This is a close-up image, texture is reported as raised or bumpy, no associated systemic symptoms reported, the affected area is the top or side of the foot, reported lesion symptoms include itching, the condition has been present for more than one year, self-categorized by the patient as a rash:
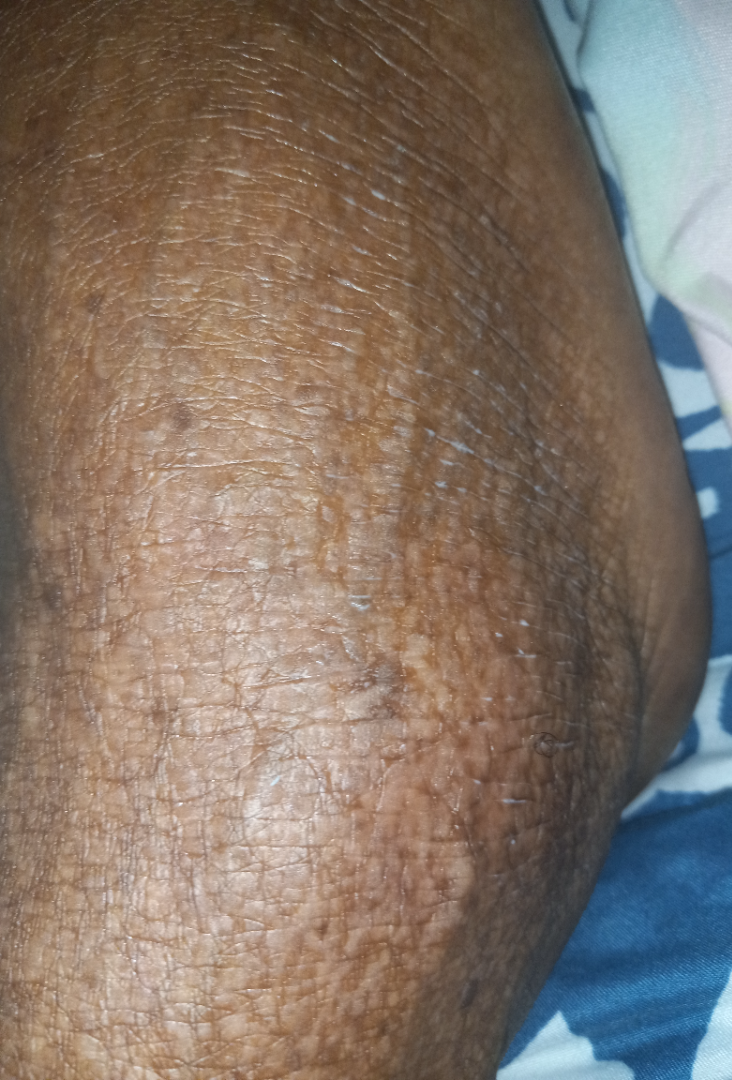The reviewing dermatologist was unable to assign a differential diagnosis from the image.